A dermoscopic photograph of a skin lesion:
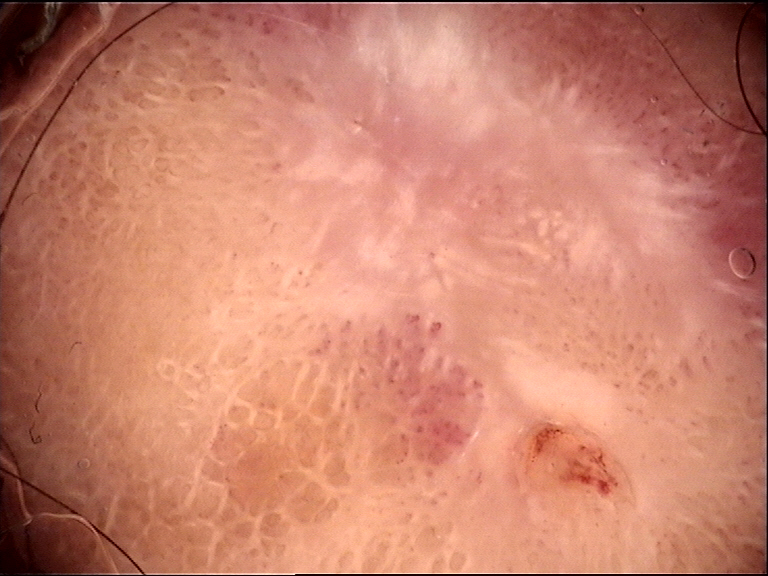This is a fibro-histiocytic lesion.
Consistent with a dermatofibroma.